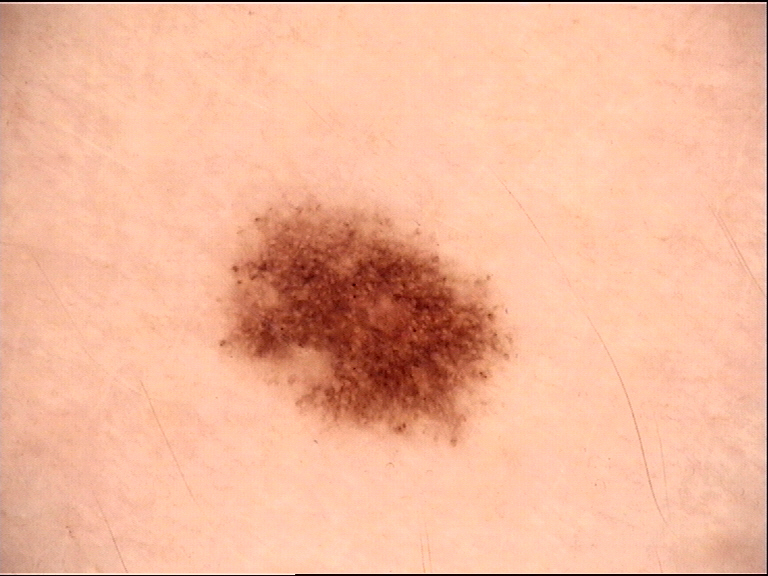imaging: dermoscopy | class: dysplastic junctional nevus (expert consensus).